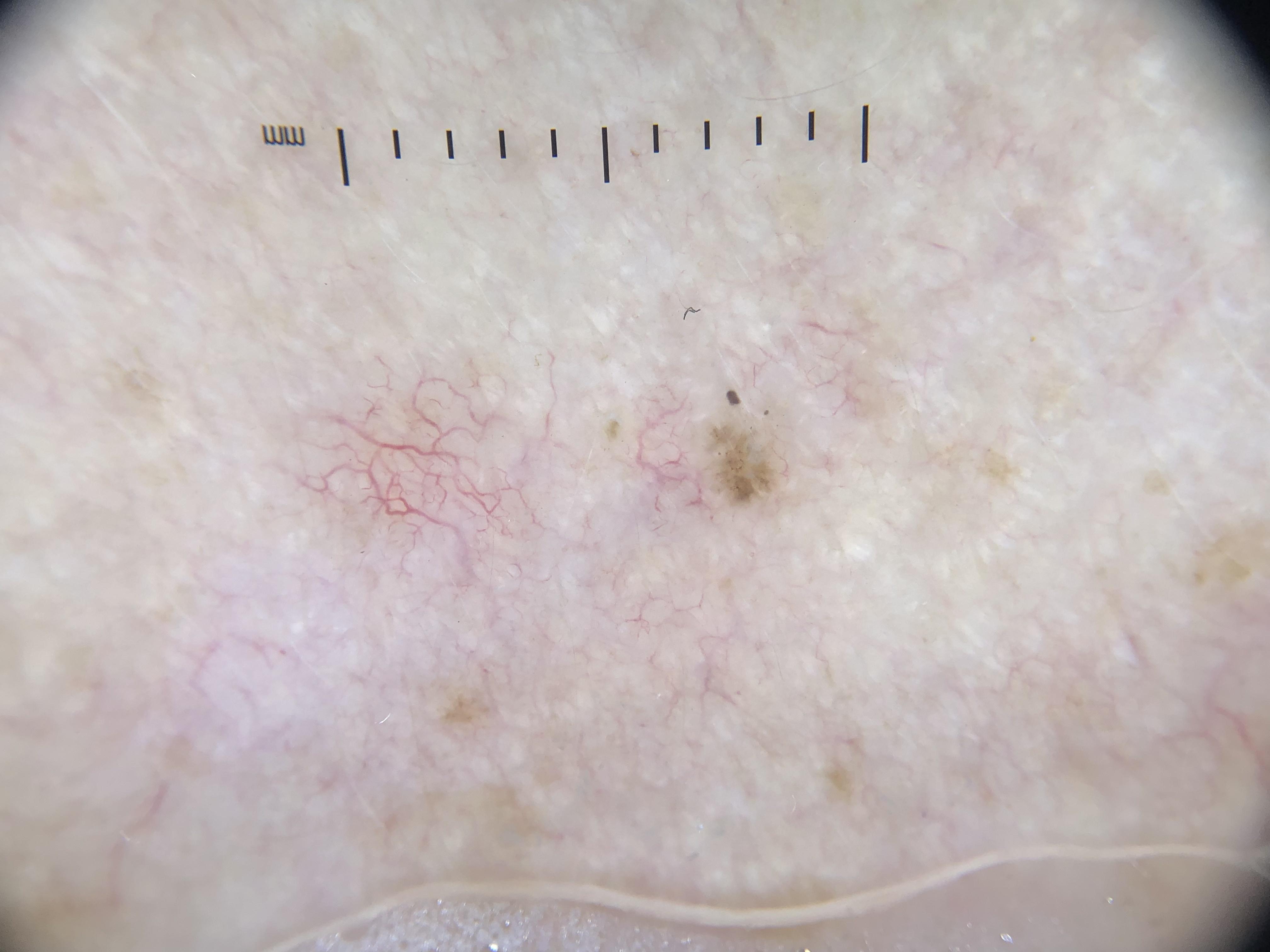Conclusion: Histopathological examination showed a basal cell carcinoma.